A skin lesion imaged with a dermatoscope, a male subject roughly 70 years of age — 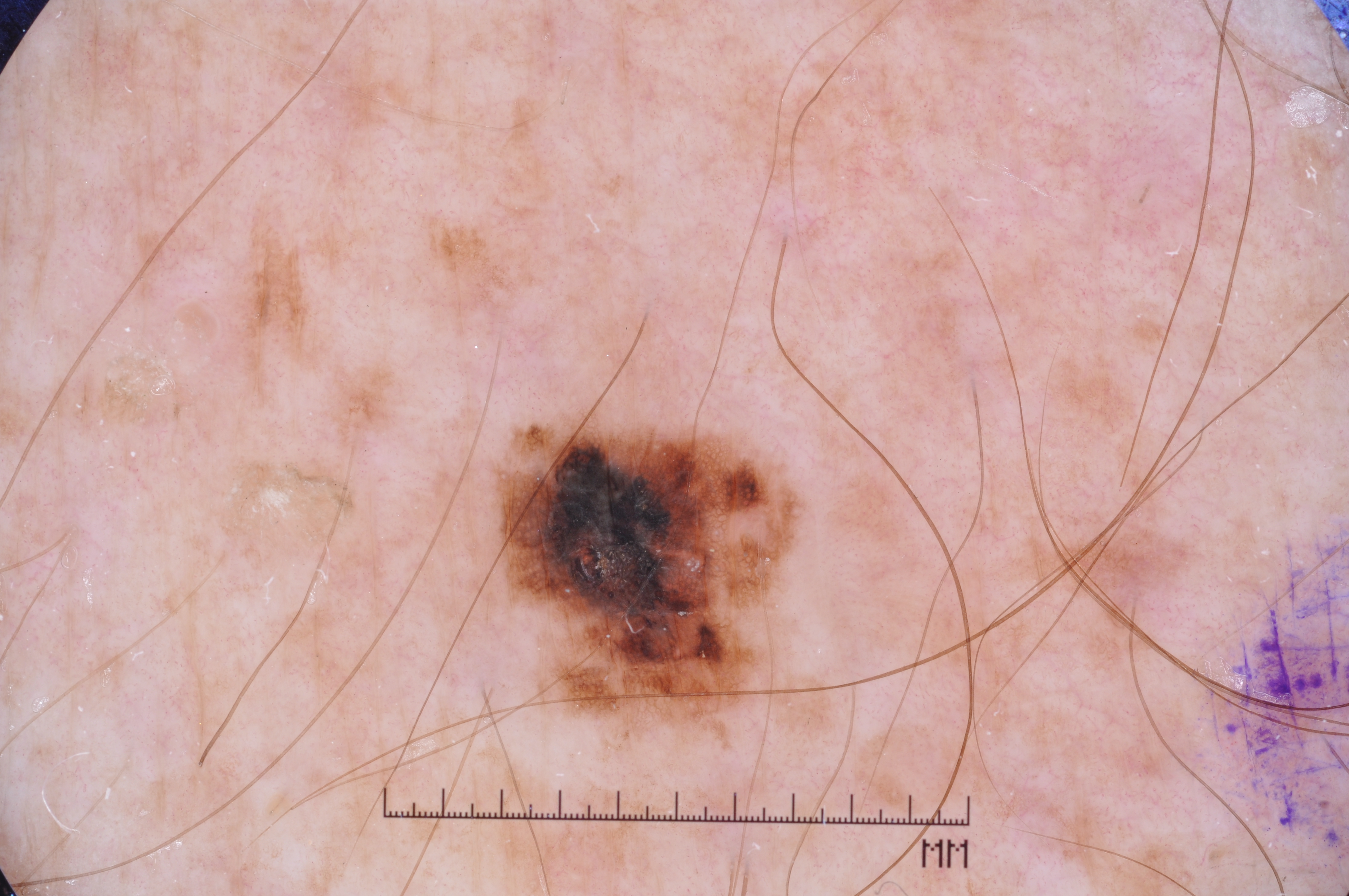The lesion is small relative to the field of view. The lesion occupies the region x1=506 y1=421 x2=780 y2=714. Dermoscopic assessment notes milia-like cysts and pigment network; no negative network or streaks. Histopathologically confirmed as a melanoma, a skin cancer.